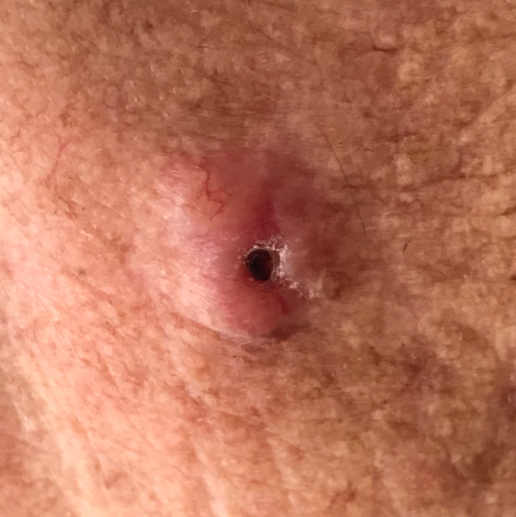{"skin_type": "II", "patient": {"age": 77, "gender": "male"}, "risk_factors": {"positive": ["prior skin cancer (patient or family)"]}, "image": "clinical photo", "lesion_location": "the neck", "lesion_size": {"diameter_1_mm": 10.0, "diameter_2_mm": 9.0}, "symptoms": {"present": ["bleeding", "itching", "elevation", "change in appearance", "growth"]}, "diagnosis": {"name": "actinic keratosis", "code": "ACK", "malignancy": "indeterminate", "confirmation": "histopathology"}}